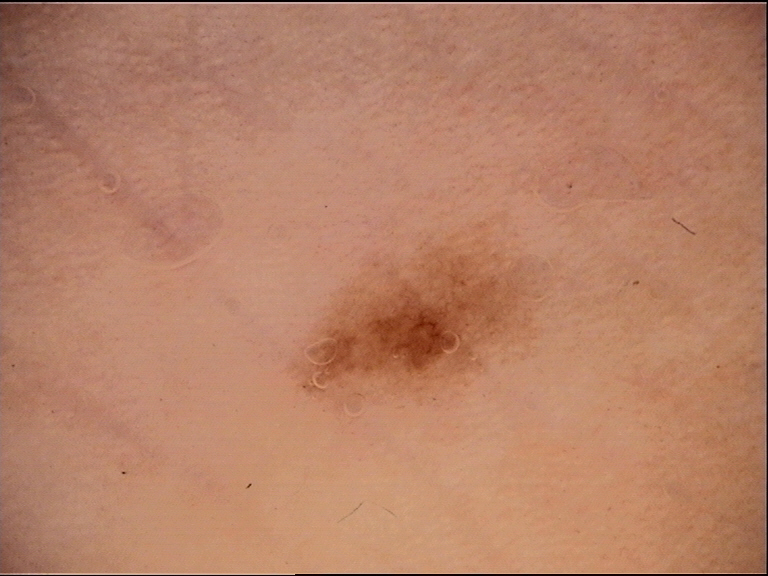diagnostic label — acral dysplastic junctional nevus (expert consensus)